A female patient aged 51 · the patient is FST II · a clinical photo of a skin lesion taken with a smartphone · the chart notes alcohol use:
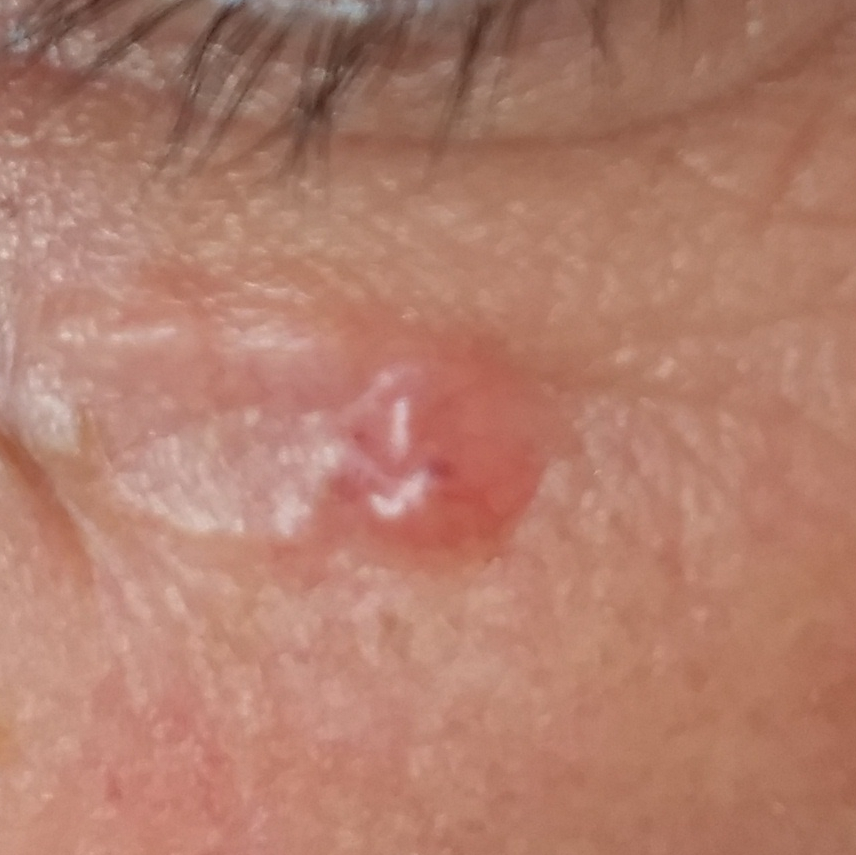Clinical context:
The lesion is located on the face. Measuring about 4 × 4 mm. The patient reports that the lesion is elevated, but has not grown and does not itch.
Conclusion:
The biopsy diagnosis was a basal cell carcinoma.